A dermoscopic photograph of a skin lesion:
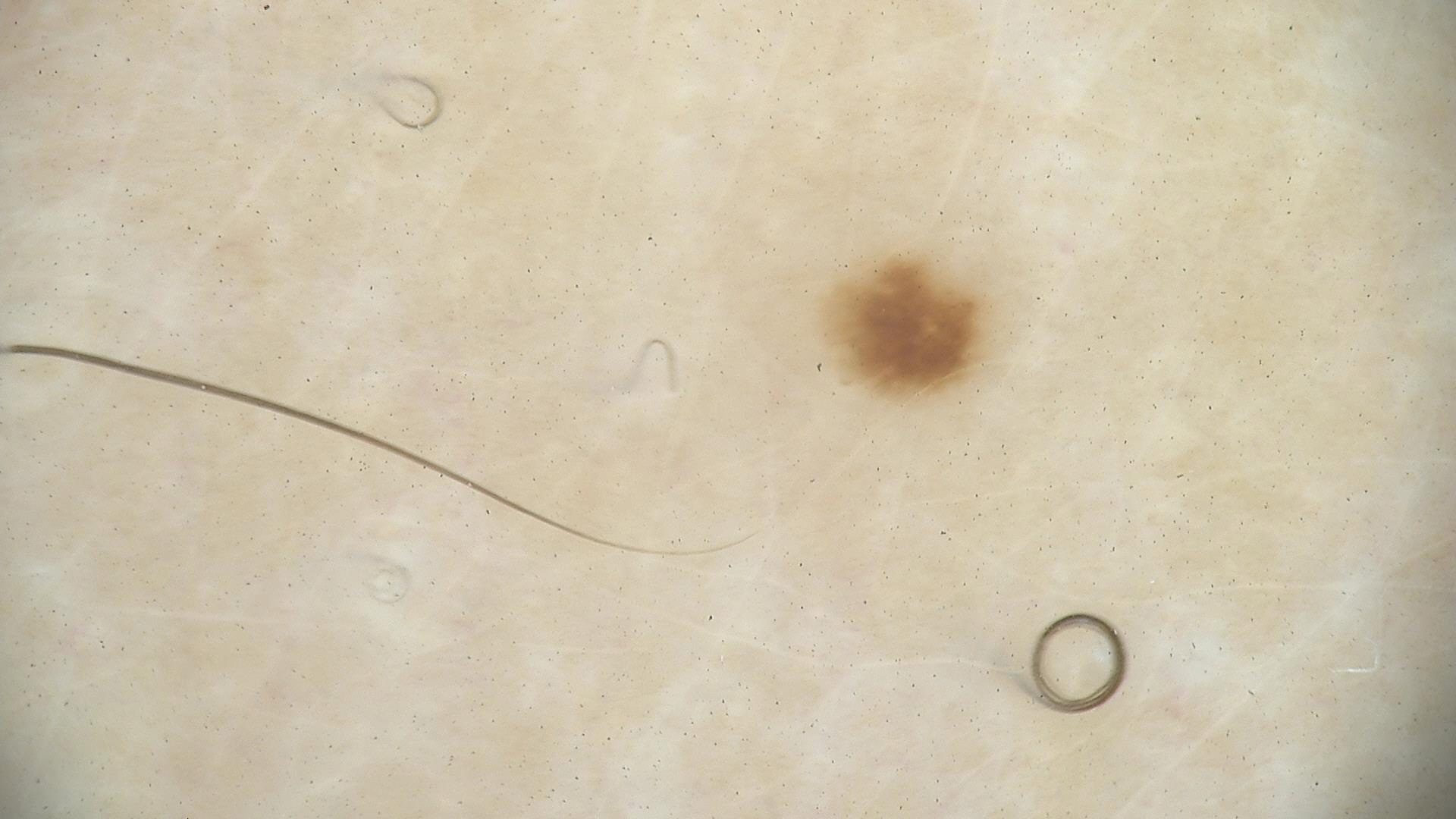Labeled as a dysplastic junctional nevus.